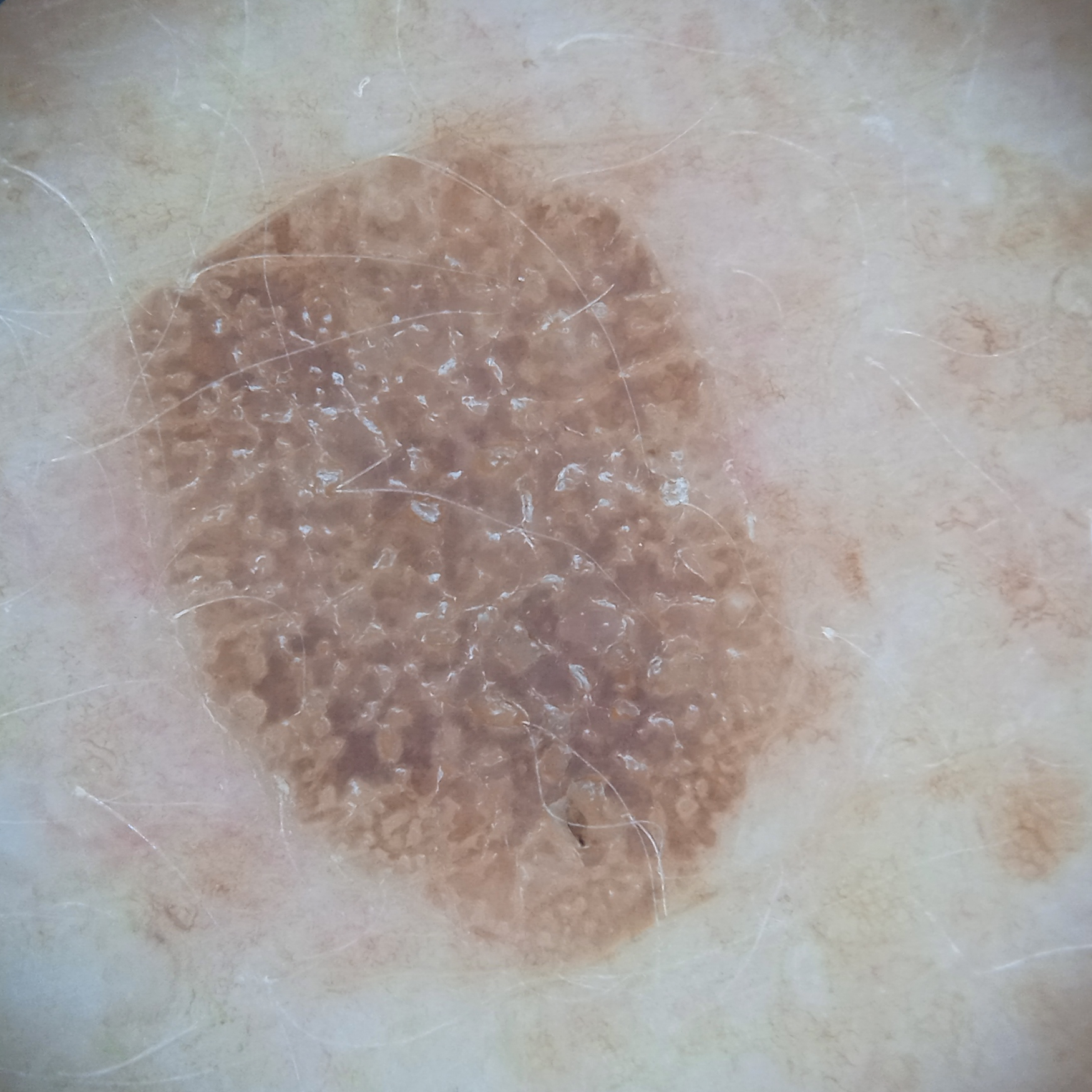The consensus diagnosis for this lesion was a seborrheic keratosis.